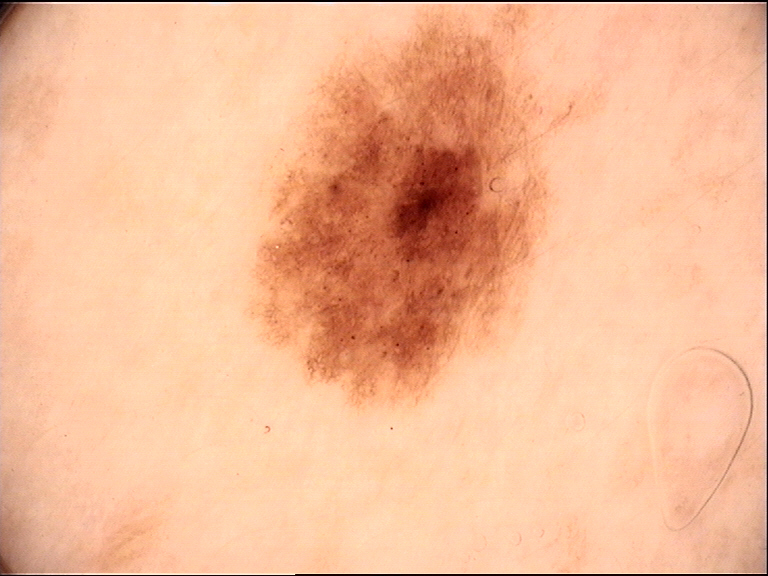{
  "image": "dermoscopy",
  "diagnosis": {
    "name": "dysplastic junctional nevus",
    "code": "jd",
    "malignancy": "benign",
    "super_class": "melanocytic",
    "confirmation": "expert consensus"
  }
}